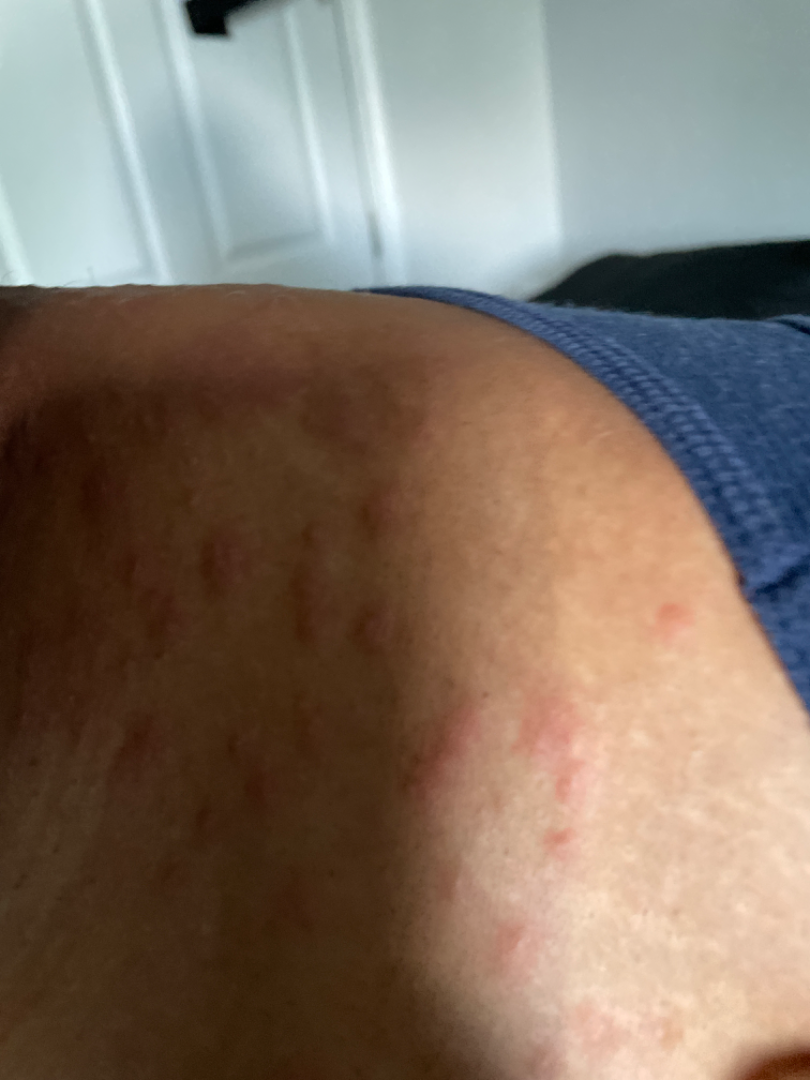view — close-up | differential — Folliculitis, Insect Bite and Allergic Contact Dermatitis were considered with similar weight.